The top or side of the foot is involved · female subject, age 30–39 · this image was taken at an angle — 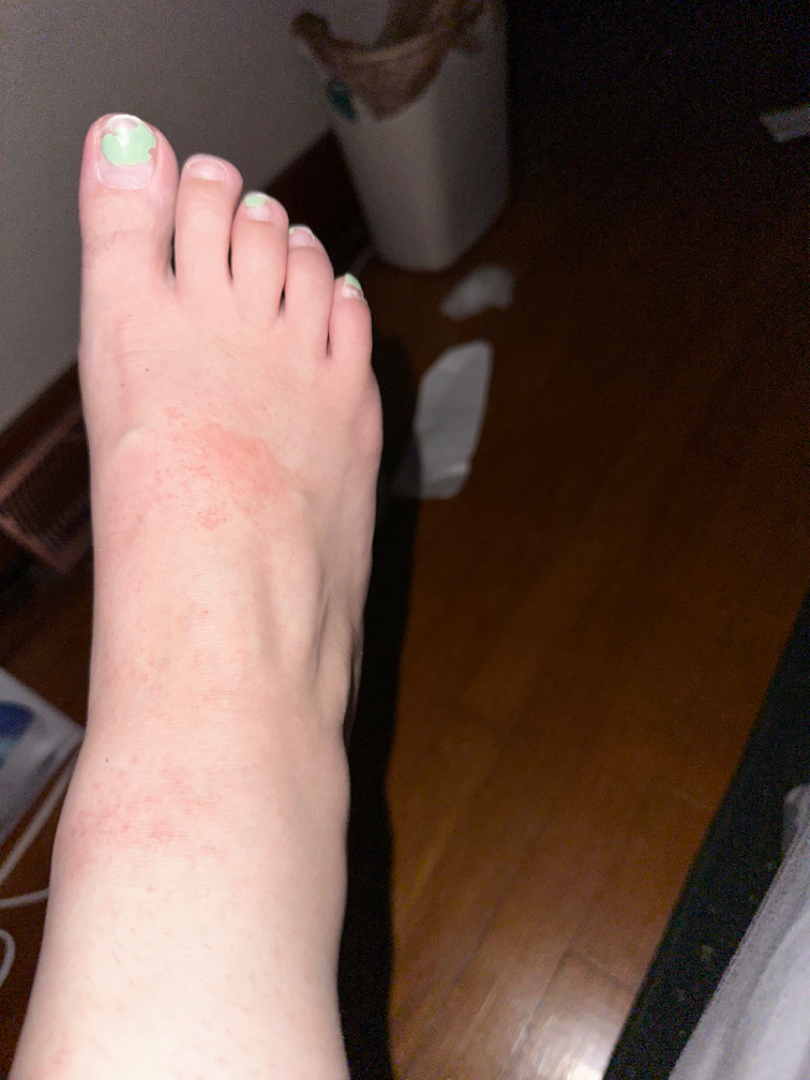<summary>
  <duration>less than one week</duration>
  <texture>raised or bumpy</texture>
  <skin_tone>
    <fitzpatrick>II</fitzpatrick>
    <monk_skin_tone>2</monk_skin_tone>
  </skin_tone>
  <patient_category>a rash</patient_category>
  <systemic_symptoms>none reported</systemic_symptoms>
  <differential>
    <tied_lead>Contact dermatitis, Eczema, Lichen Simplex Chronicus, Allergic Contact Dermatitis</tied_lead>
    <unlikely>Pigmented purpuric eruption</unlikely>
  </differential>
</summary>